The lesion is described as raised or bumpy and rough or flaky. An image taken at an angle. Self-categorized by the patient as a rash. The affected area is the head or neck. Reported duration is more than five years — 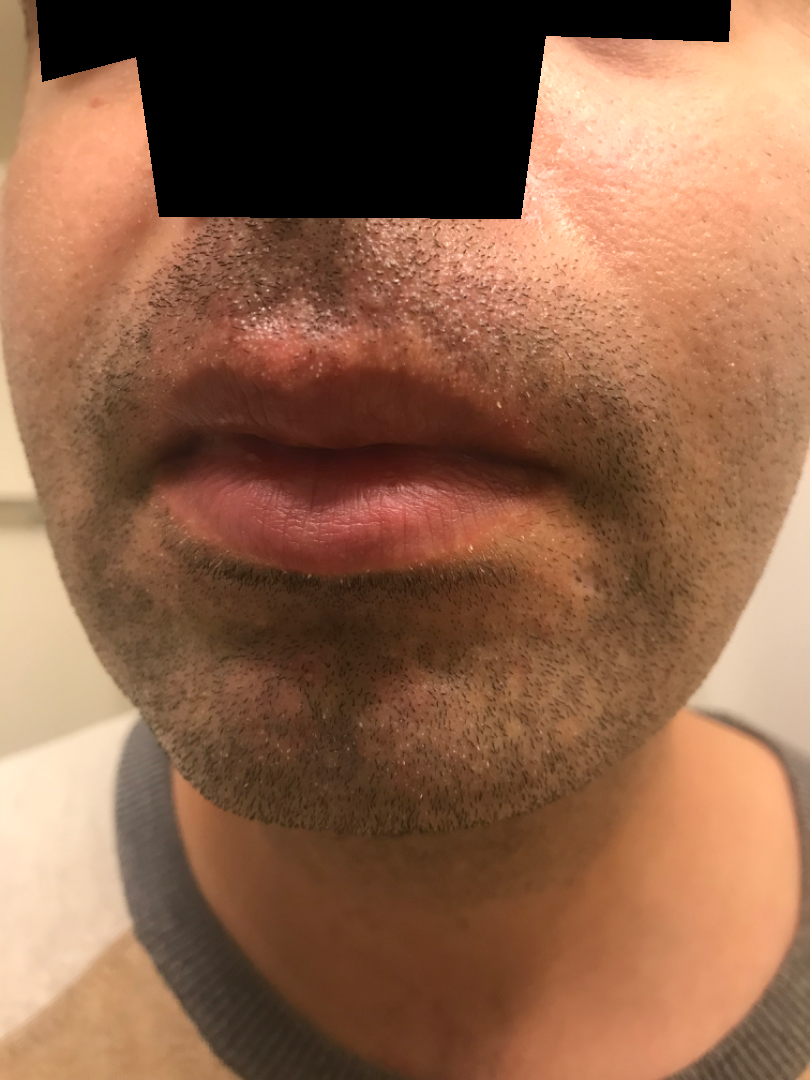assessment: indeterminate.